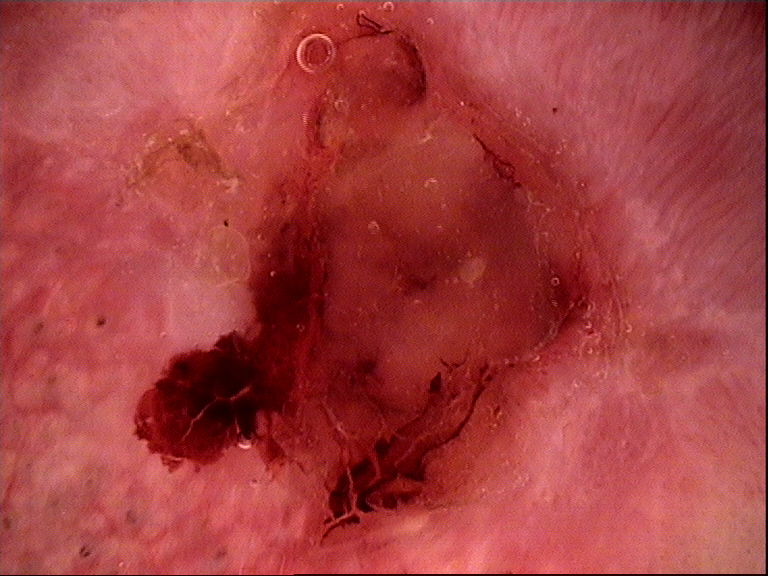A dermoscopic image of a skin lesion. Histopathology confirmed a malignant, keratinocytic lesion — a squamous cell carcinoma.